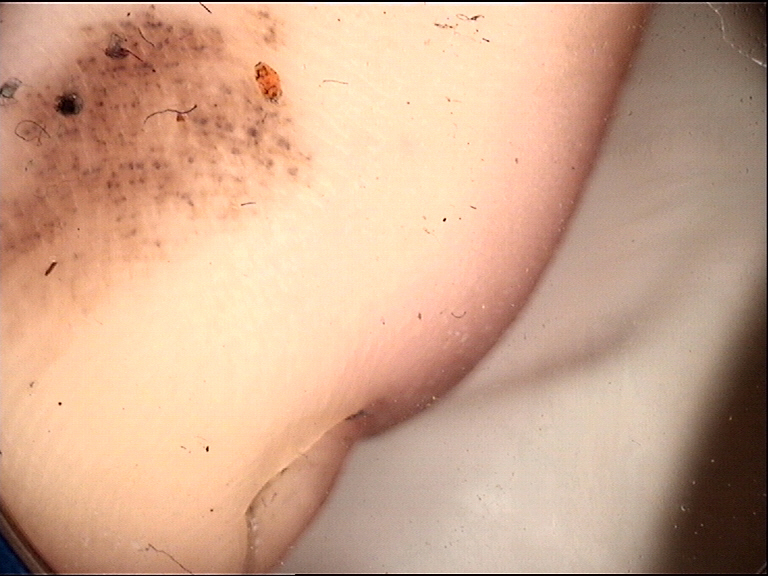Q: What kind of image is this?
A: dermatoscopy
Q: What is this lesion?
A: acral junctional nevus (expert consensus)